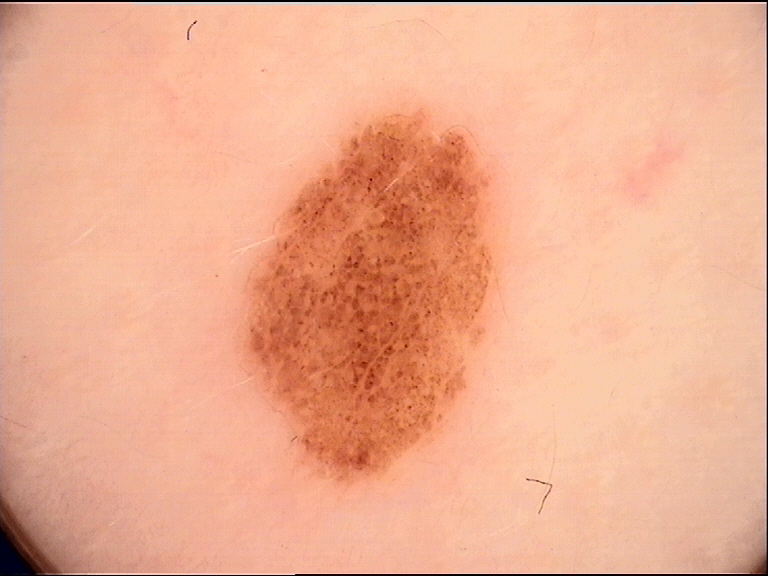Case:
Dermoscopy of a skin lesion.
Conclusion:
Labeled as a benign lesion — a dysplastic junctional nevus.